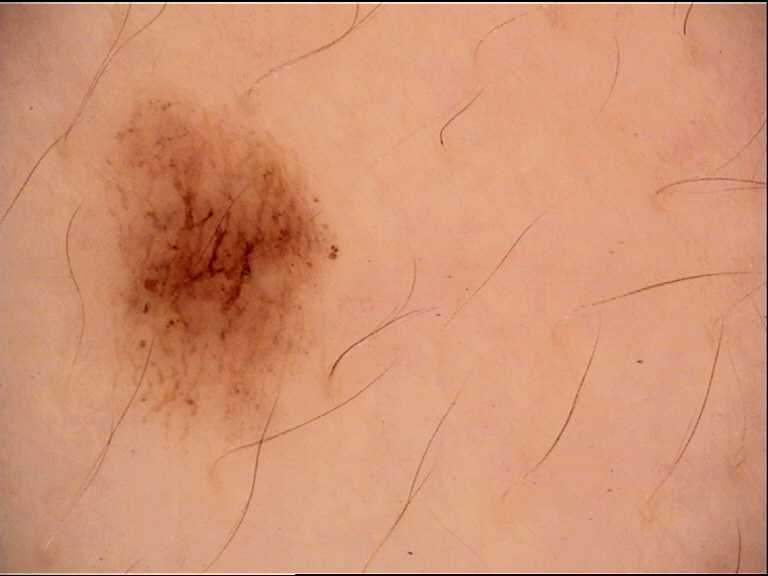imaging: dermoscopy
diagnosis: dysplastic junctional nevus (expert consensus)